The photograph is a close-up of the affected area:
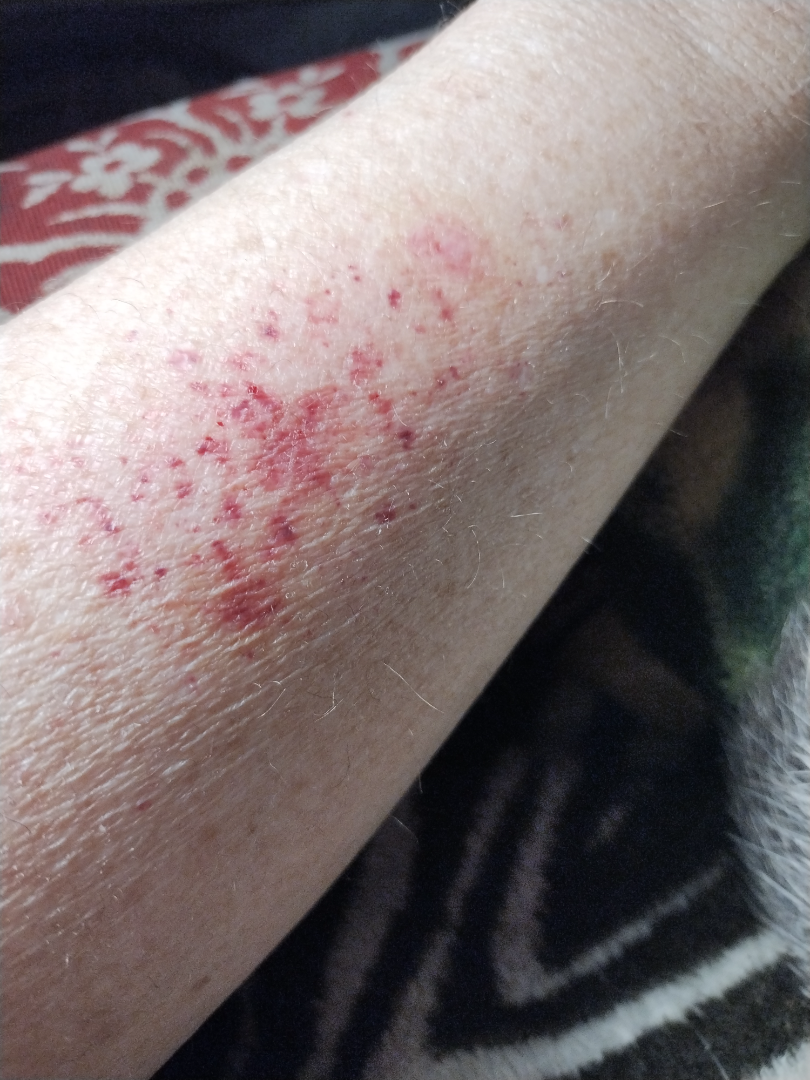The reviewing clinician's impression was: ecchymoses (most likely).